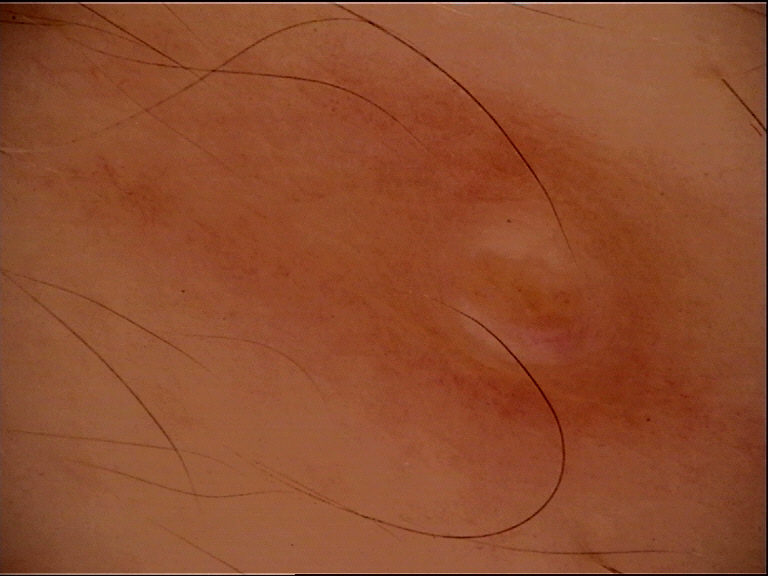Case:
• imaging — dermoscopy
• label — dermal nevus (expert consensus)